The patient is Fitzpatrick II. Contact-polarized dermoscopy of a skin lesion. A female subject roughly 50 years of age.
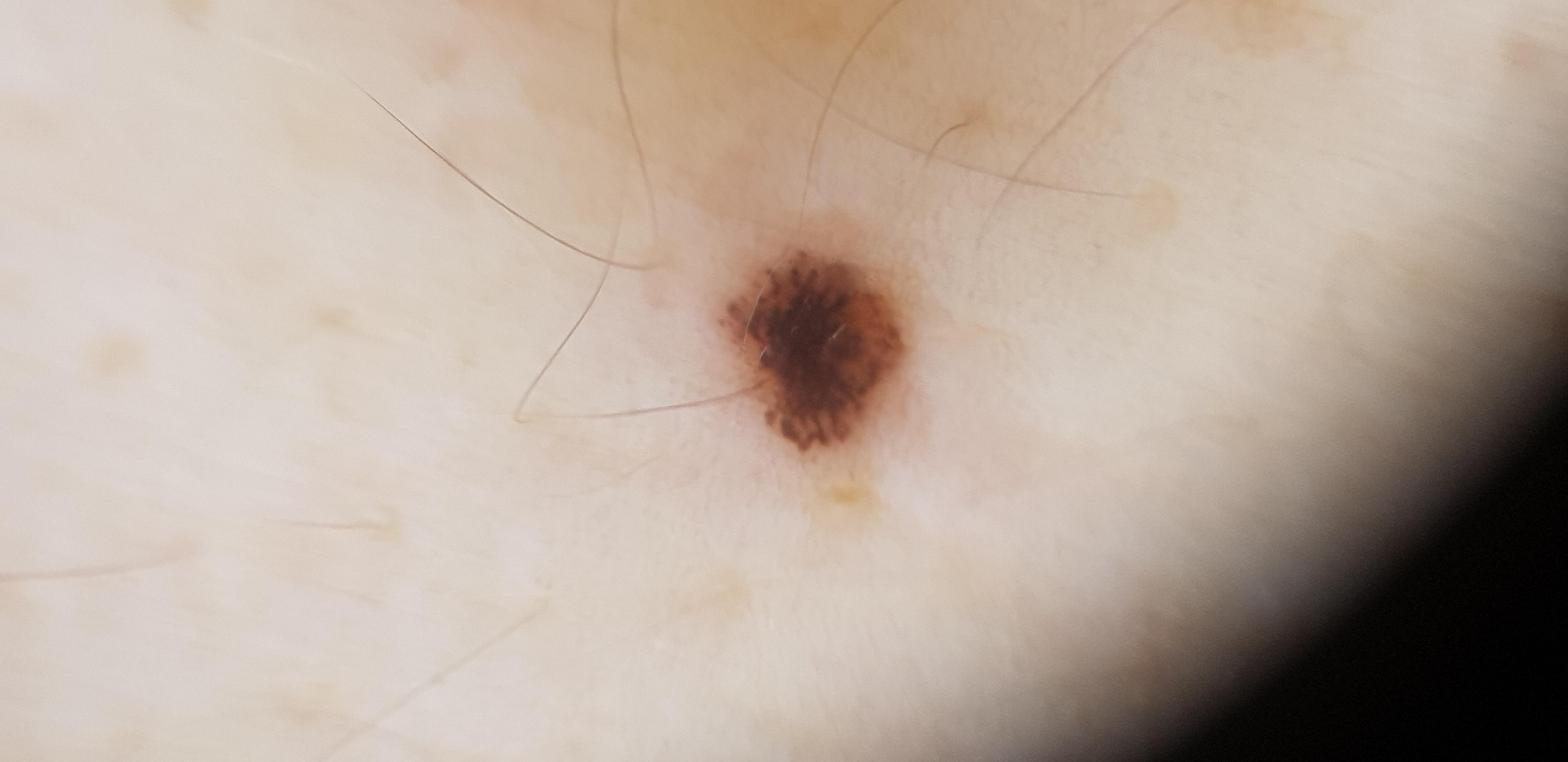The lesion is located on the posterior trunk. The biopsy diagnosis was a benign lesion — a nevus.